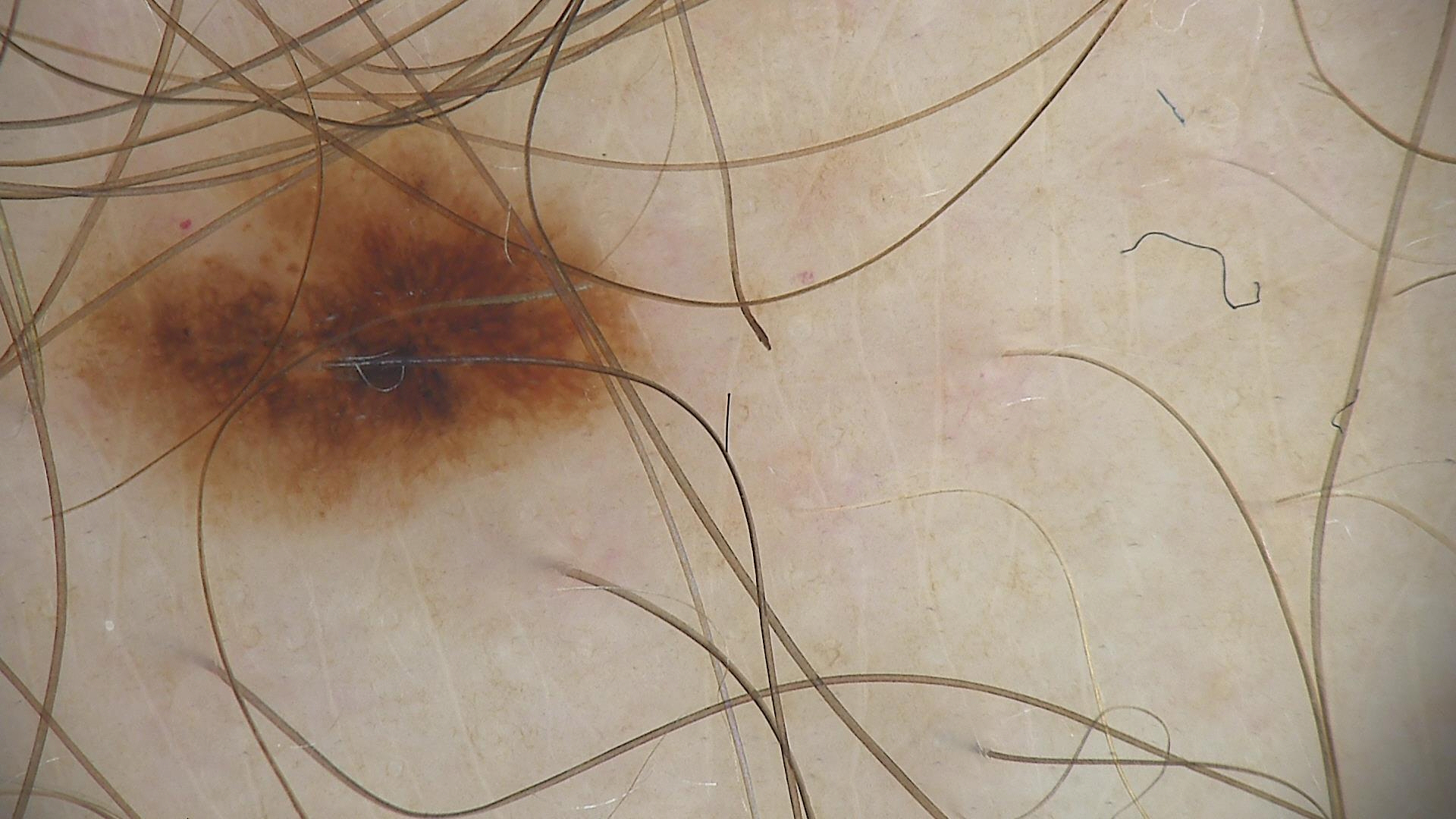A dermoscopic image of a skin lesion. The diagnostic label was a benign lesion — a dysplastic junctional nevus.